The subject is 50–59, female · the photo was captured at an angle · located on the leg — 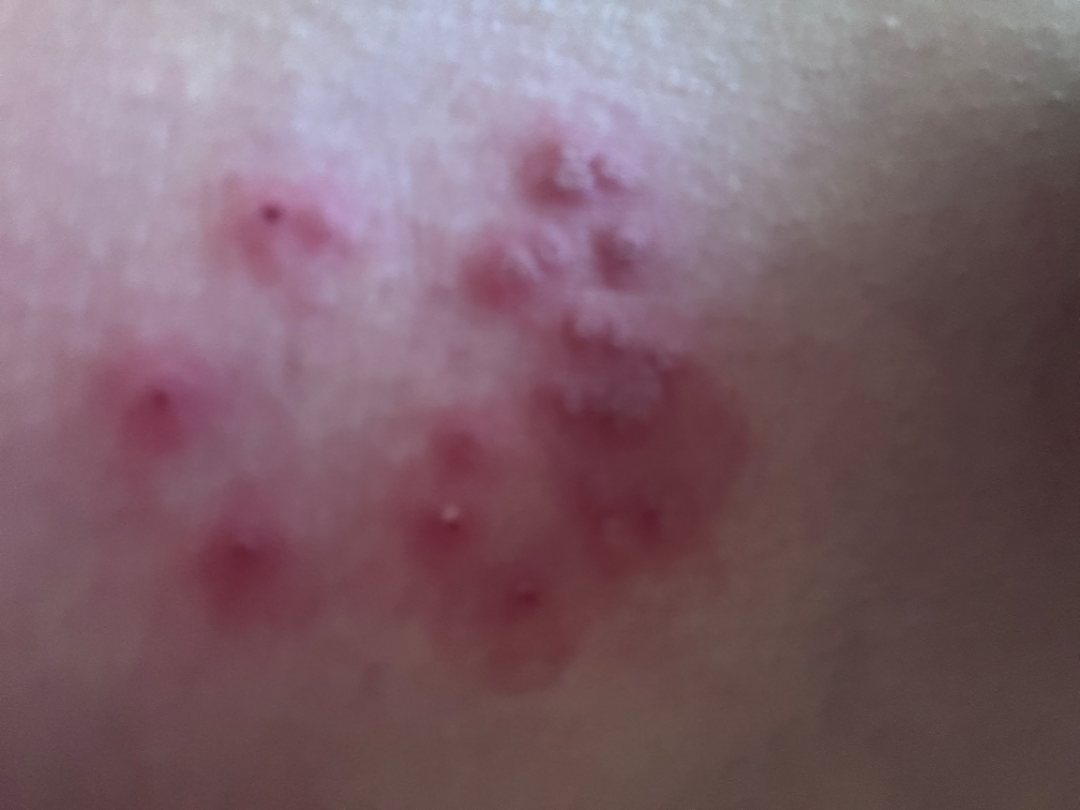Reviewed remotely by one dermatologist: the leading impression is Molluscum Contagiosum; also on the differential is Impetigo; an alternative is Herpes Simplex.